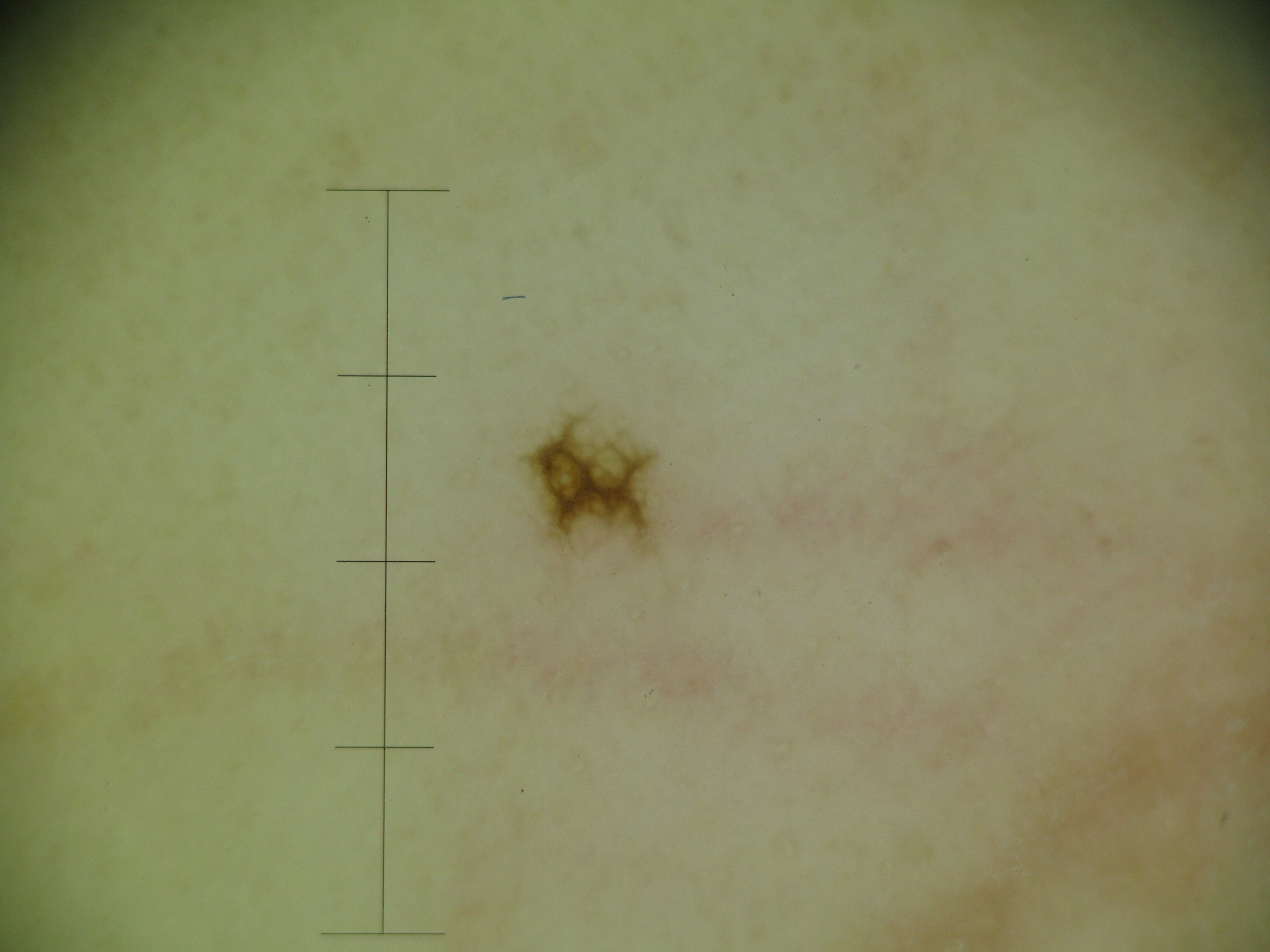A dermatoscopic image of a skin lesion.
The architecture is that of a banal lesion.
Consistent with an acral junctional nevus.